The patient describes having few moles overall. The patient says their skin tans without first burning. Dermoscopy of a skin lesion.
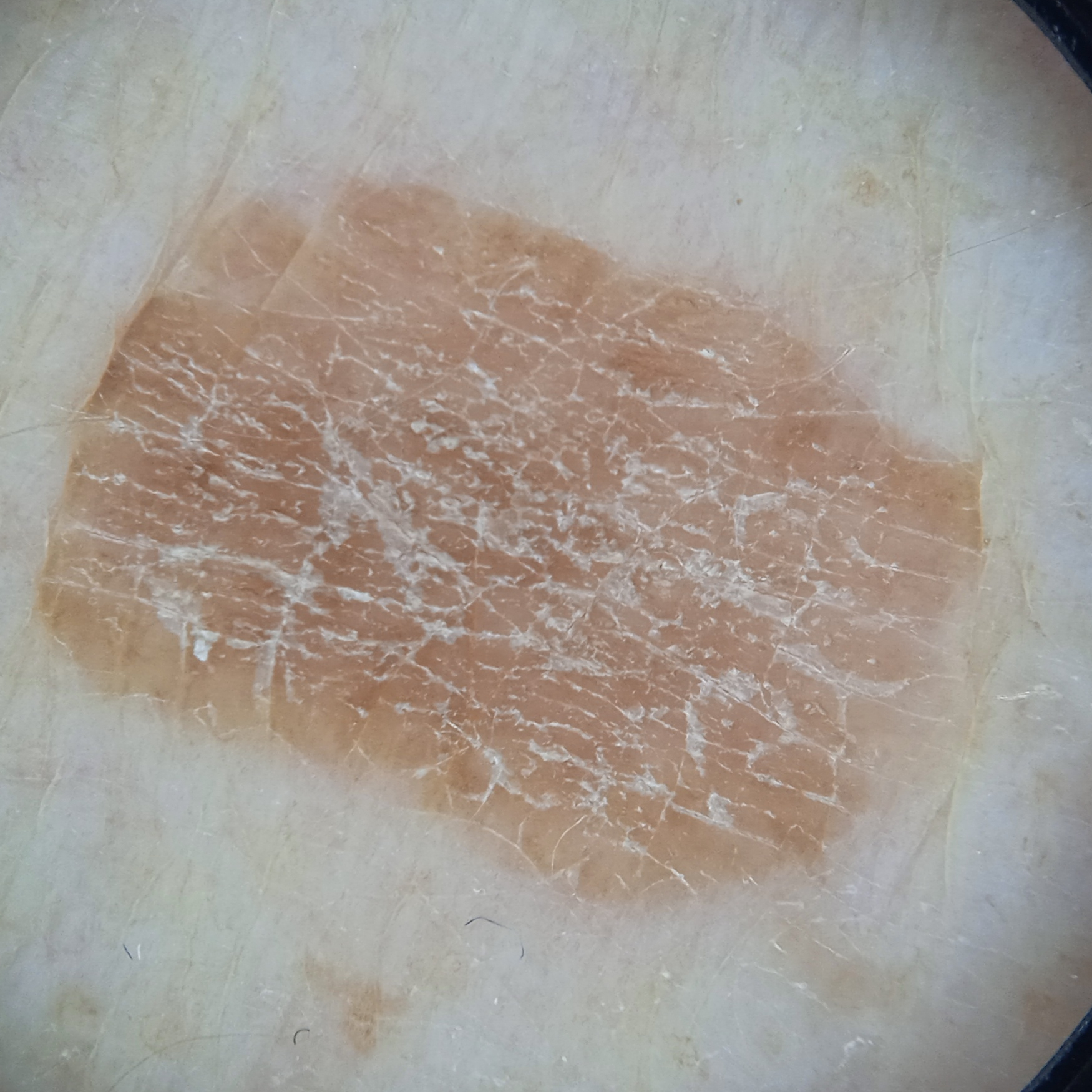  lesion_size:
    diameter_mm: 11.2
  diagnosis:
    name: seborrheic keratosis
    malignancy: benign